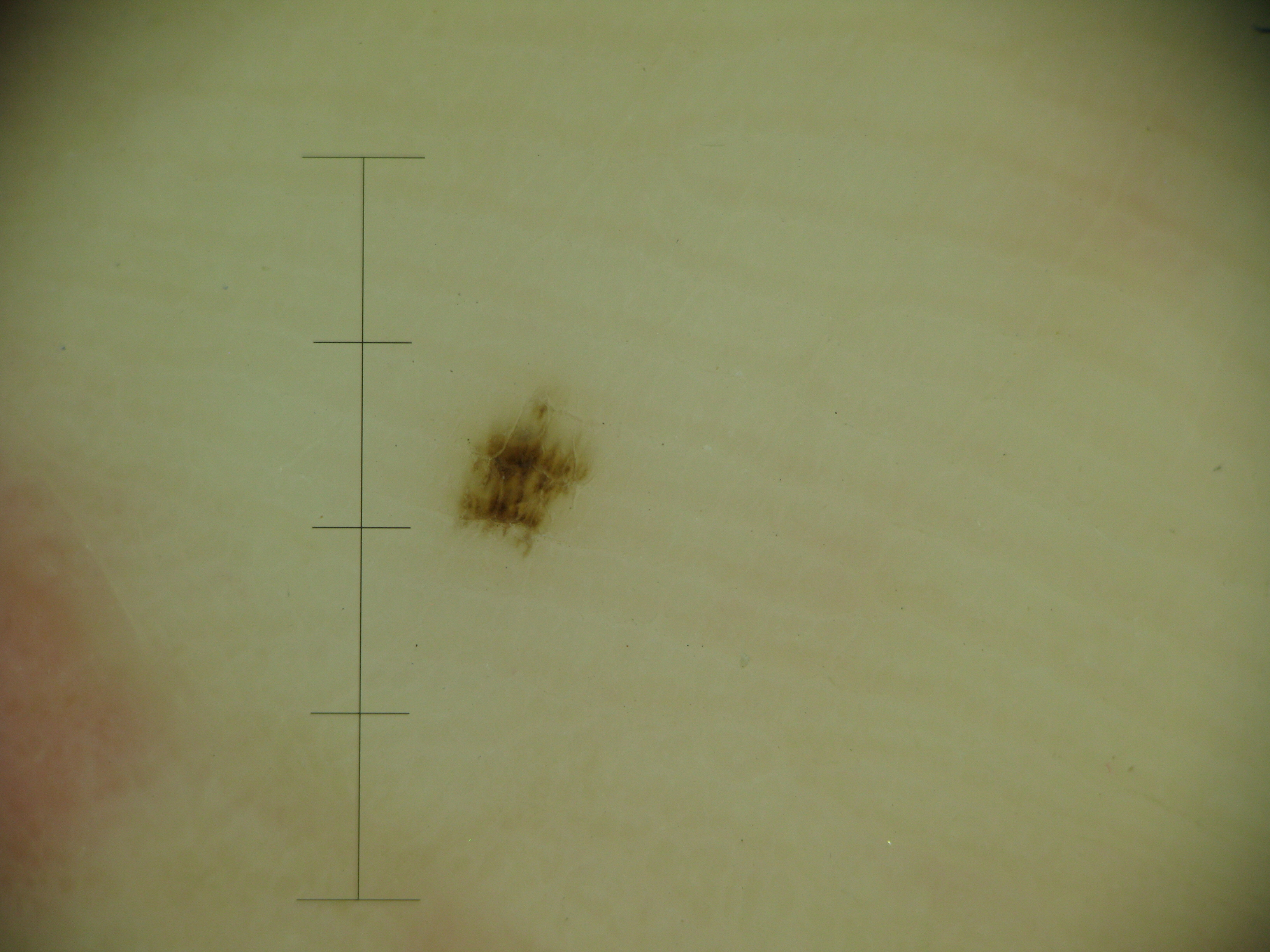modality: dermatoscopy | label: acral dysplastic junctional nevus (expert consensus).